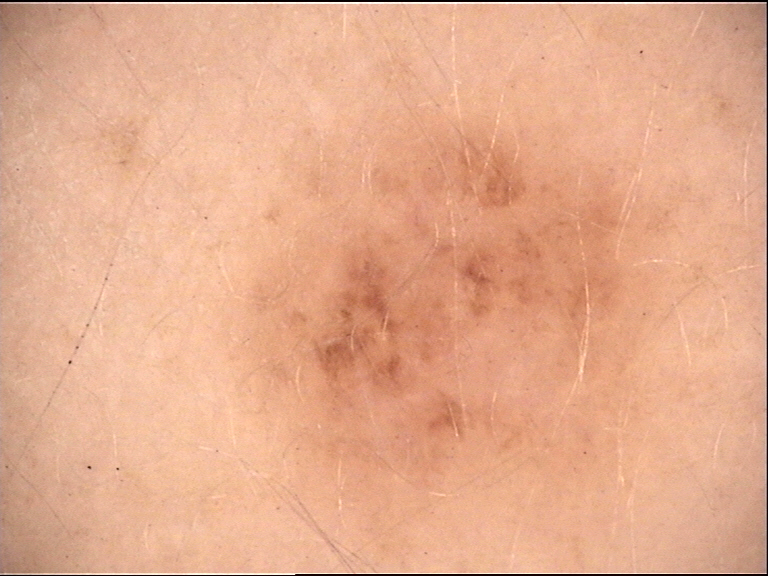Consistent with a dermal nevus.